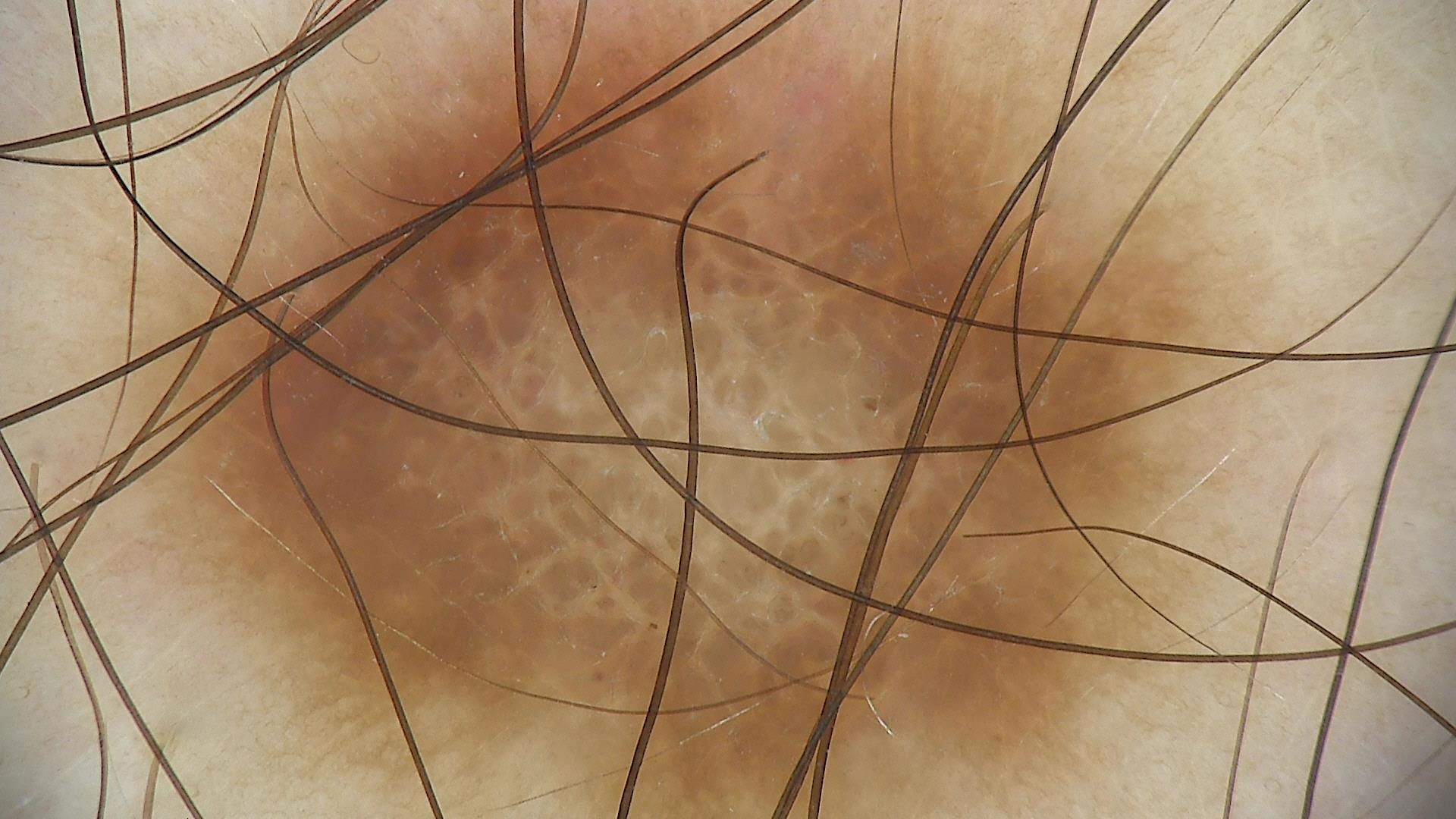Case:
- modality: dermoscopy
- subtype: fibro-histiocytic
- class: dermatofibroma (expert consensus)